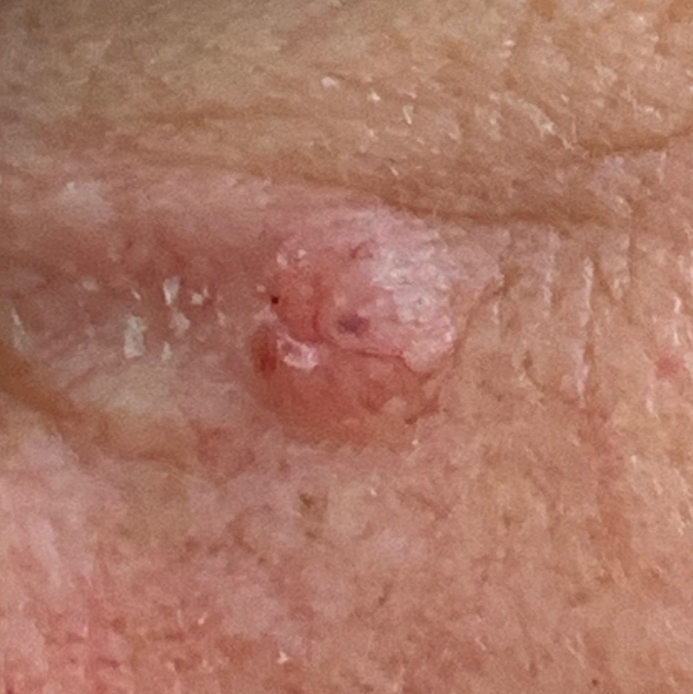{
  "risk_factors": {
    "positive": [
      "alcohol use"
    ]
  },
  "image": "clinical photograph",
  "lesion_location": "the face",
  "lesion_size": {
    "diameter_1_mm": 4.0,
    "diameter_2_mm": 4.0
  },
  "symptoms": {
    "present": [
      "elevation"
    ]
  },
  "diagnosis": {
    "name": "basal cell carcinoma",
    "code": "BCC",
    "malignancy": "malignant",
    "confirmation": "histopathology"
  }
}